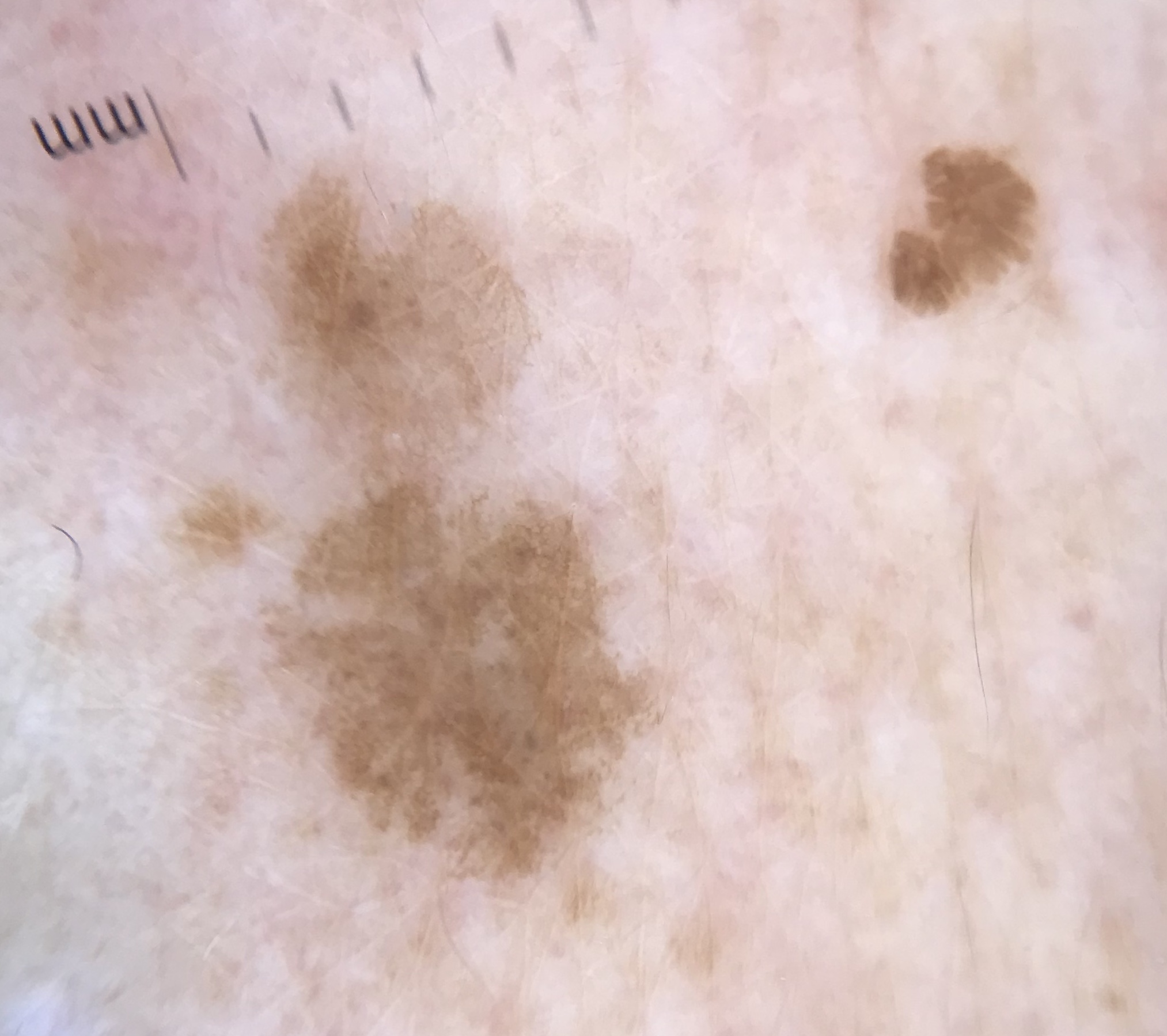A dermoscopic close-up of a skin lesion. This is a keratinocytic lesion. The diagnosis was a seborrheic keratosis.